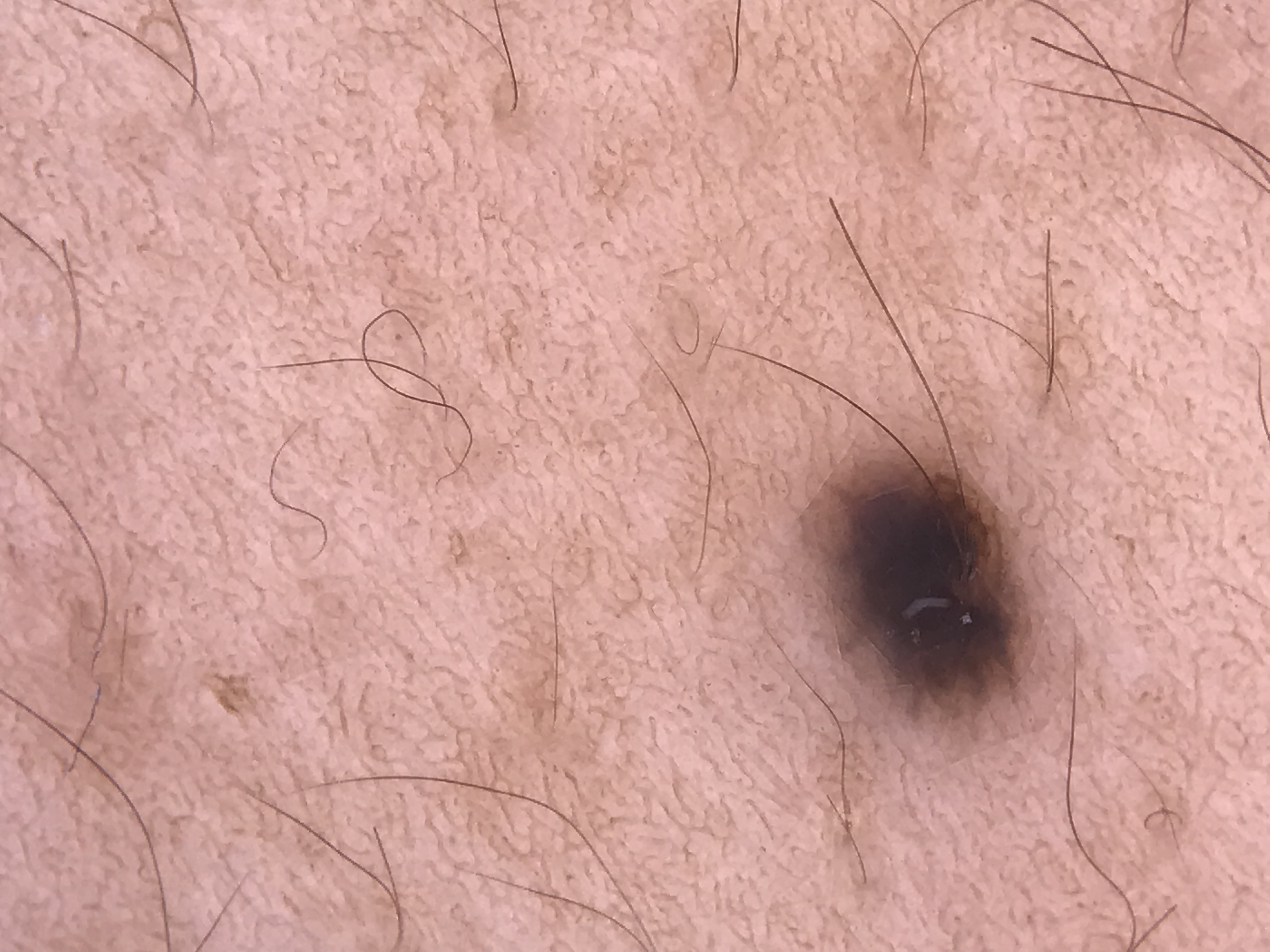Case:
Dermoscopy of a skin lesion.
Conclusion:
Classified as a dermal lesion — a blue nevus.